The lesion involves the arm. This image was taken at a distance. The patient is 18–29, male: 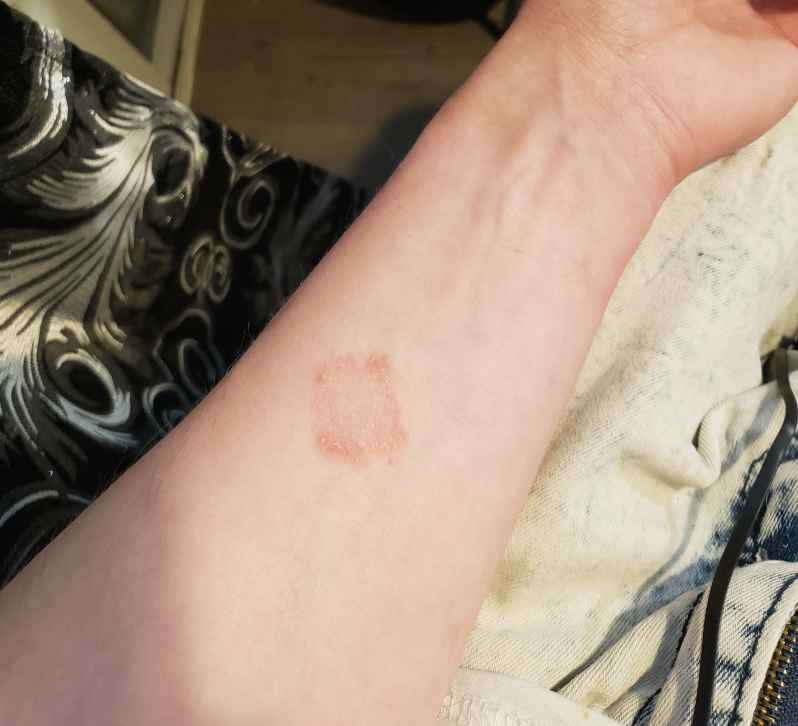Q: What is the dermatologist's impression?
A: Eczema and Tinea were each considered, in no particular order